The photo was captured at an angle · texture is reported as flat: 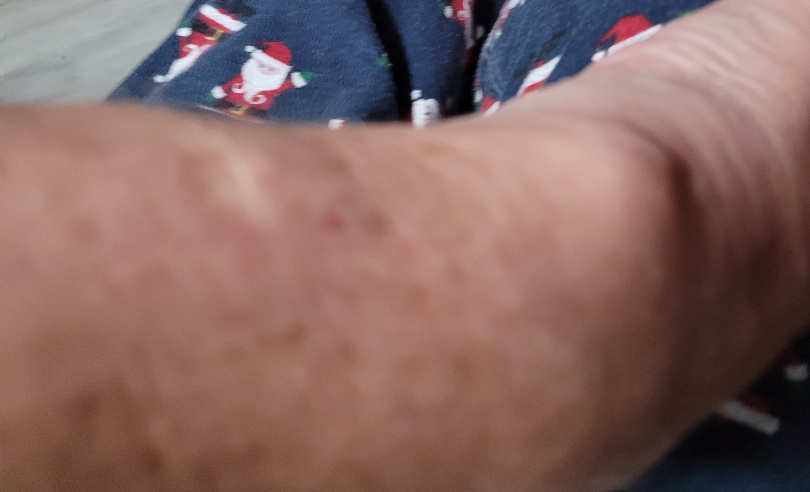assessment: indeterminate from the photograph